A female patient, approximately 80 years of age · a dermoscopic image of a skin lesion — 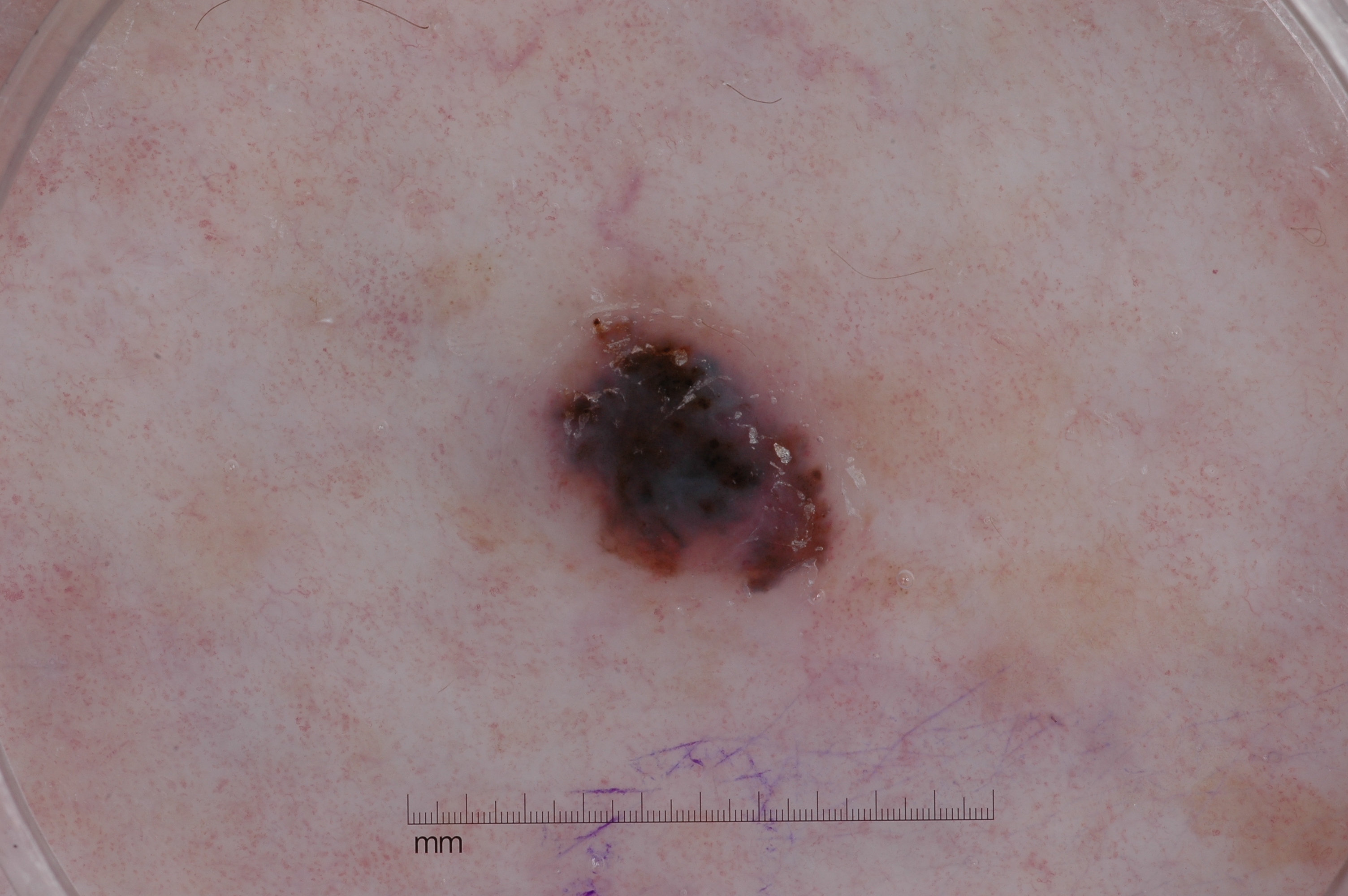bounding box=<box>527, 266, 842, 602</box>
absent dermoscopic features=milia-like cysts, streaks, pigment network, and negative network
lesion size=~6% of the field
impression=a melanoma, a skin cancer